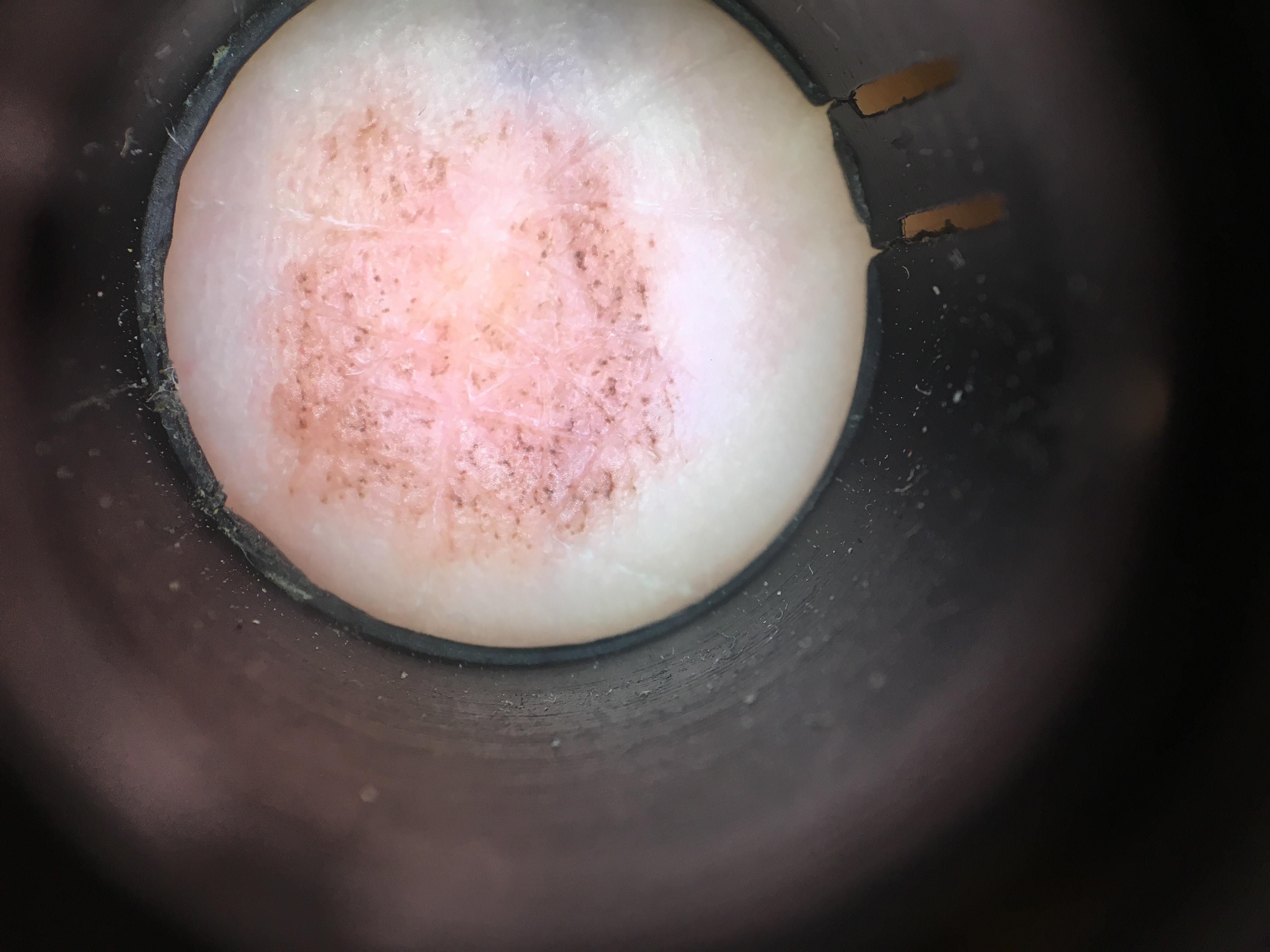Q: Who is the patient?
A: female, in their 60s
Q: Skin phototype?
A: II
Q: What kind of image is this?
A: dermoscopic image
Q: Any relevant melanoma history?
A: a prior melanoma
Q: What is the anatomic site?
A: an acral site (palms or soles)
Q: What is this lesion?
A: Nevus (biopsy-proven)